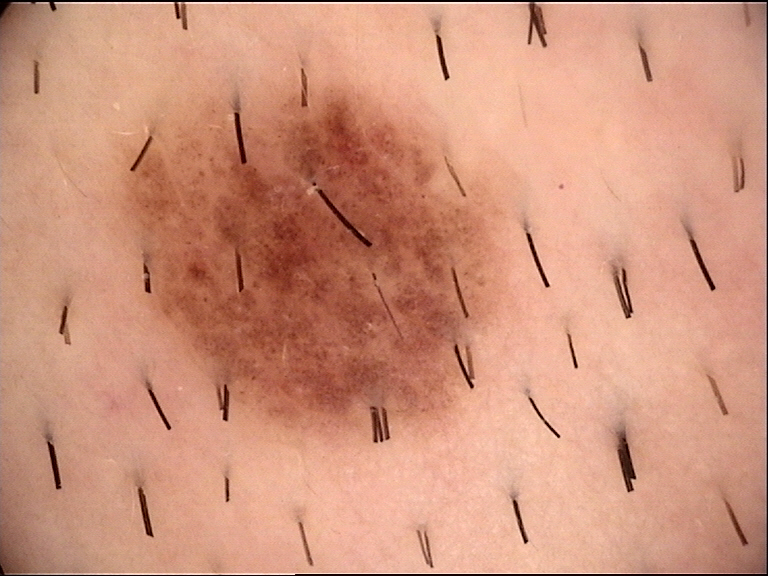A skin lesion imaged with a dermatoscope. The diagnosis was a dysplastic compound nevus.